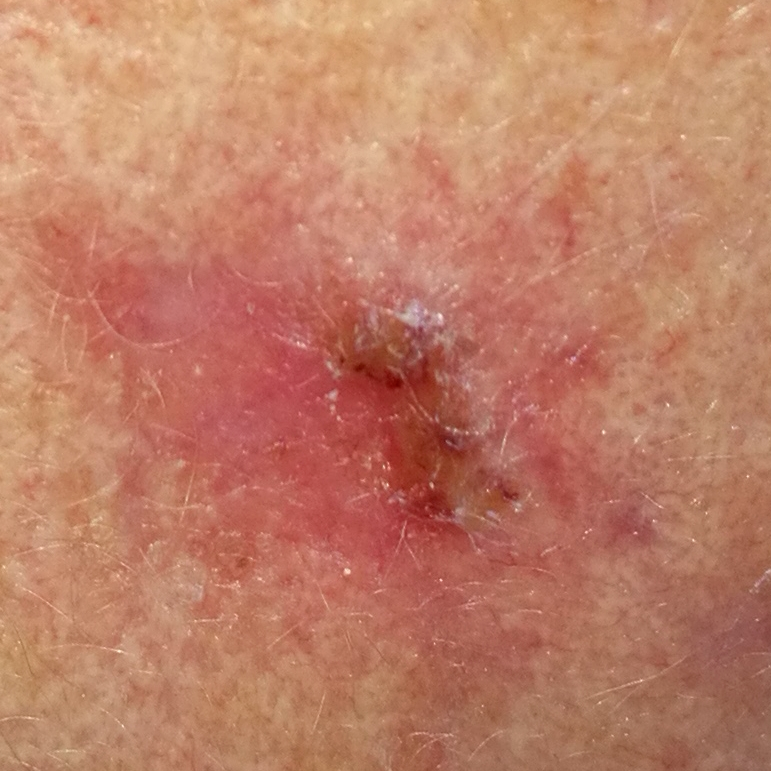The patient was assessed as FST II. By history, tobacco use, prior skin cancer (patient or family), and prior malignancy (patient or family). A female subject age 62. A smartphone photograph of a skin lesion. The lesion is located on the face. The lesion measures approximately 10 × 6 mm. On biopsy, the diagnosis was a basal cell carcinoma.